A dermoscopic photograph of a skin lesion.
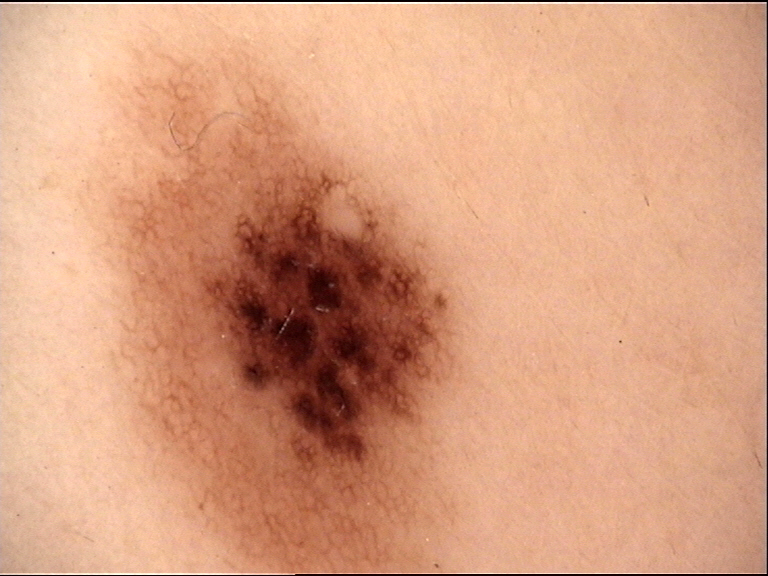{"diagnosis": {"name": "dysplastic junctional nevus", "code": "jd", "malignancy": "benign", "super_class": "melanocytic", "confirmation": "expert consensus"}}